This image was taken at a distance; the lesion involves the head or neck:
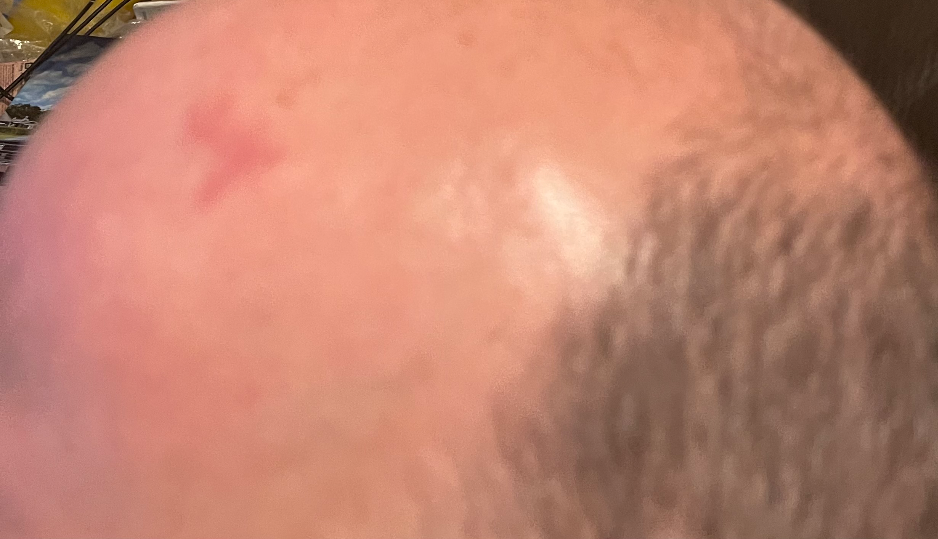Impression:
Diagnostic features were not clearly distinguishable in this photograph.